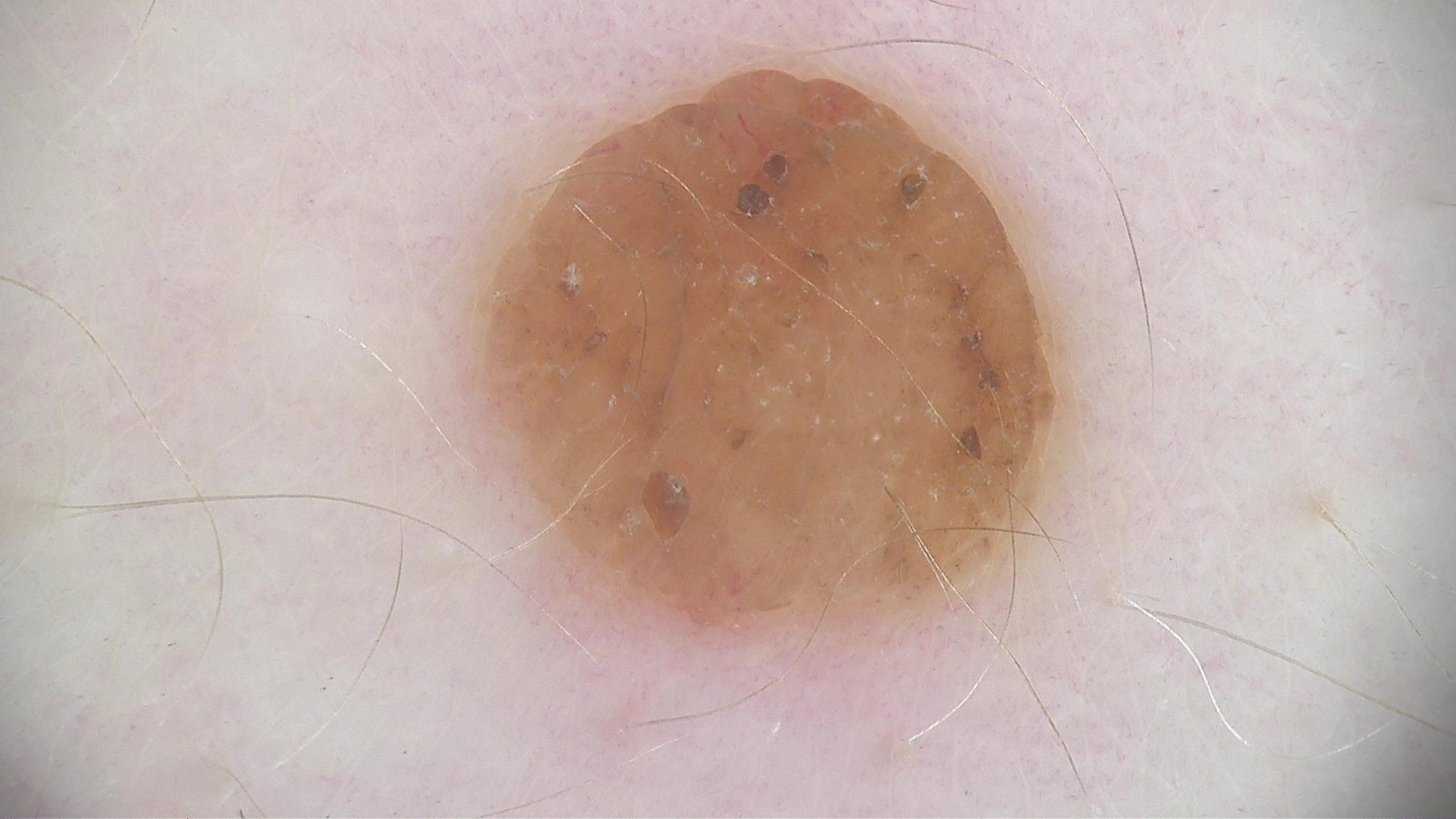{
  "lesion_type": {
    "main_class": "banal",
    "pattern": "dermal"
  },
  "diagnosis": {
    "name": "dermal nevus",
    "code": "db",
    "malignancy": "benign",
    "super_class": "melanocytic",
    "confirmation": "expert consensus"
  }
}